A female subject, about 65 years old. A dermatoscopic image of a skin lesion: 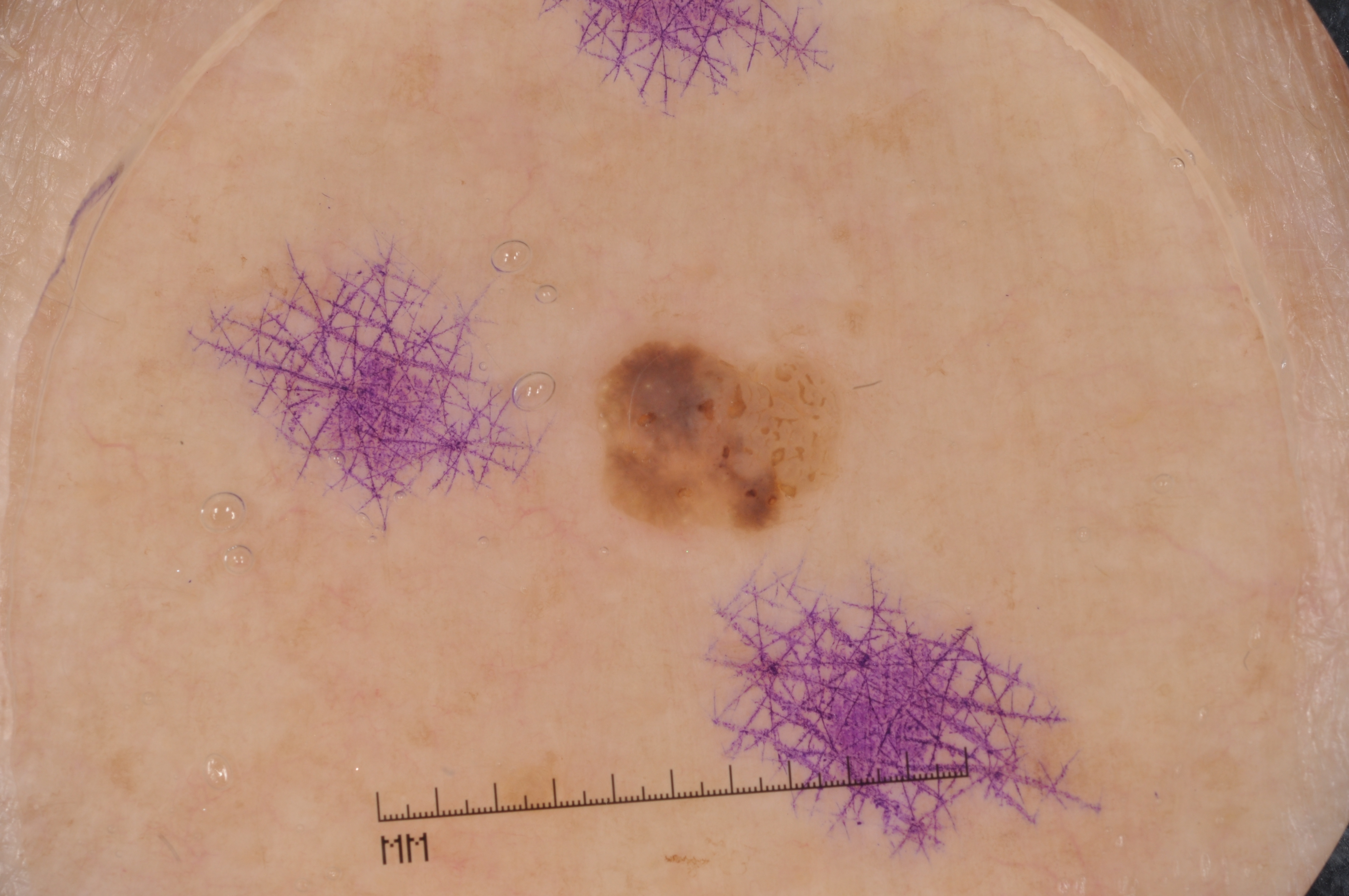Dermoscopic review identifies milia-like cysts, with no streaks, negative network, or pigment network. As (left, top, right, bottom), the lesion is bounded by <box>586, 305, 882, 546</box>. The lesion covers approximately 4% of the dermoscopic field. Diagnosed as a seborrheic keratosis.